A dermoscopic close-up of a skin lesion.
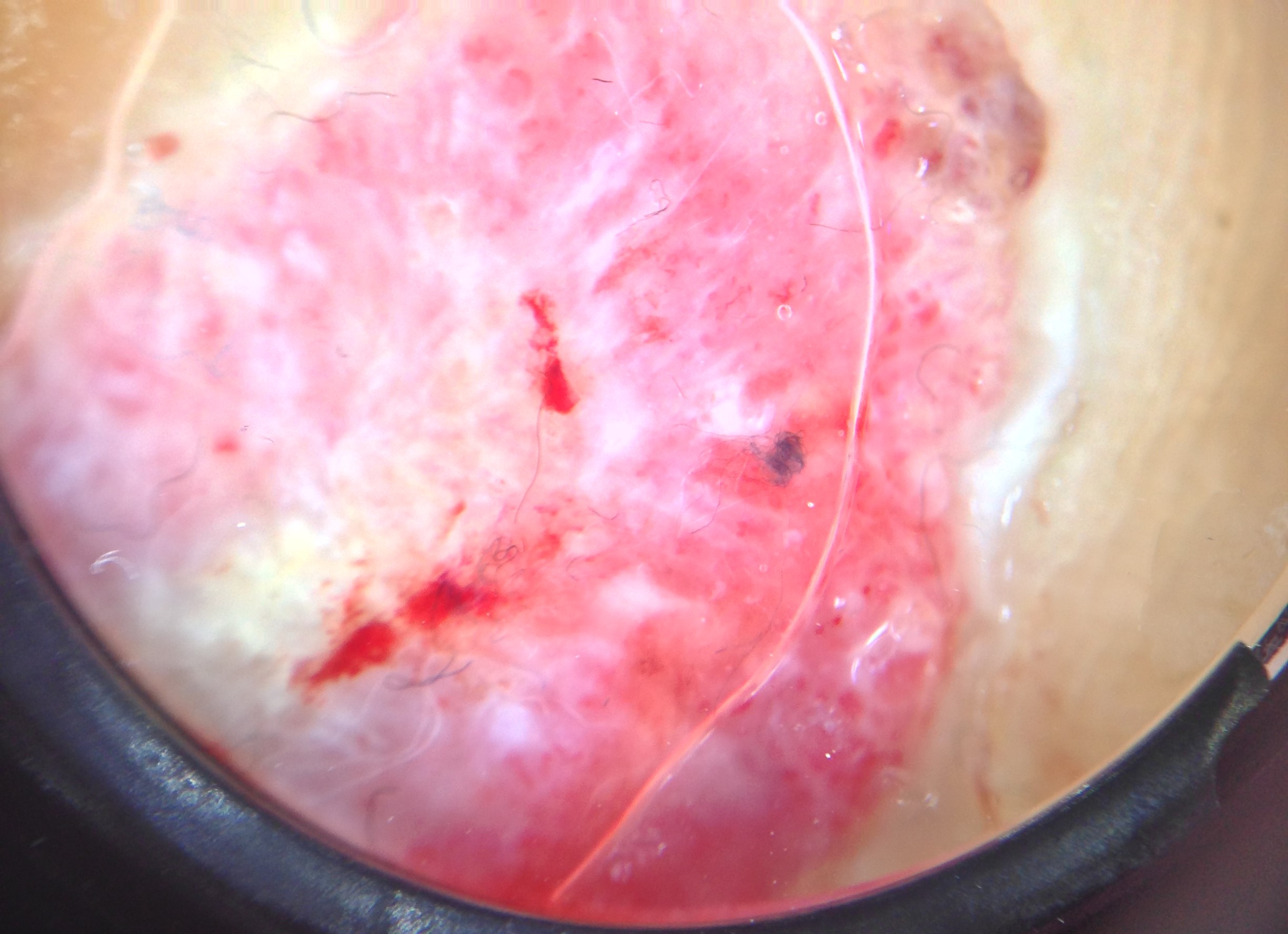class: acral nodular melanoma (biopsy-proven).